Dermoscopy of a skin lesion: 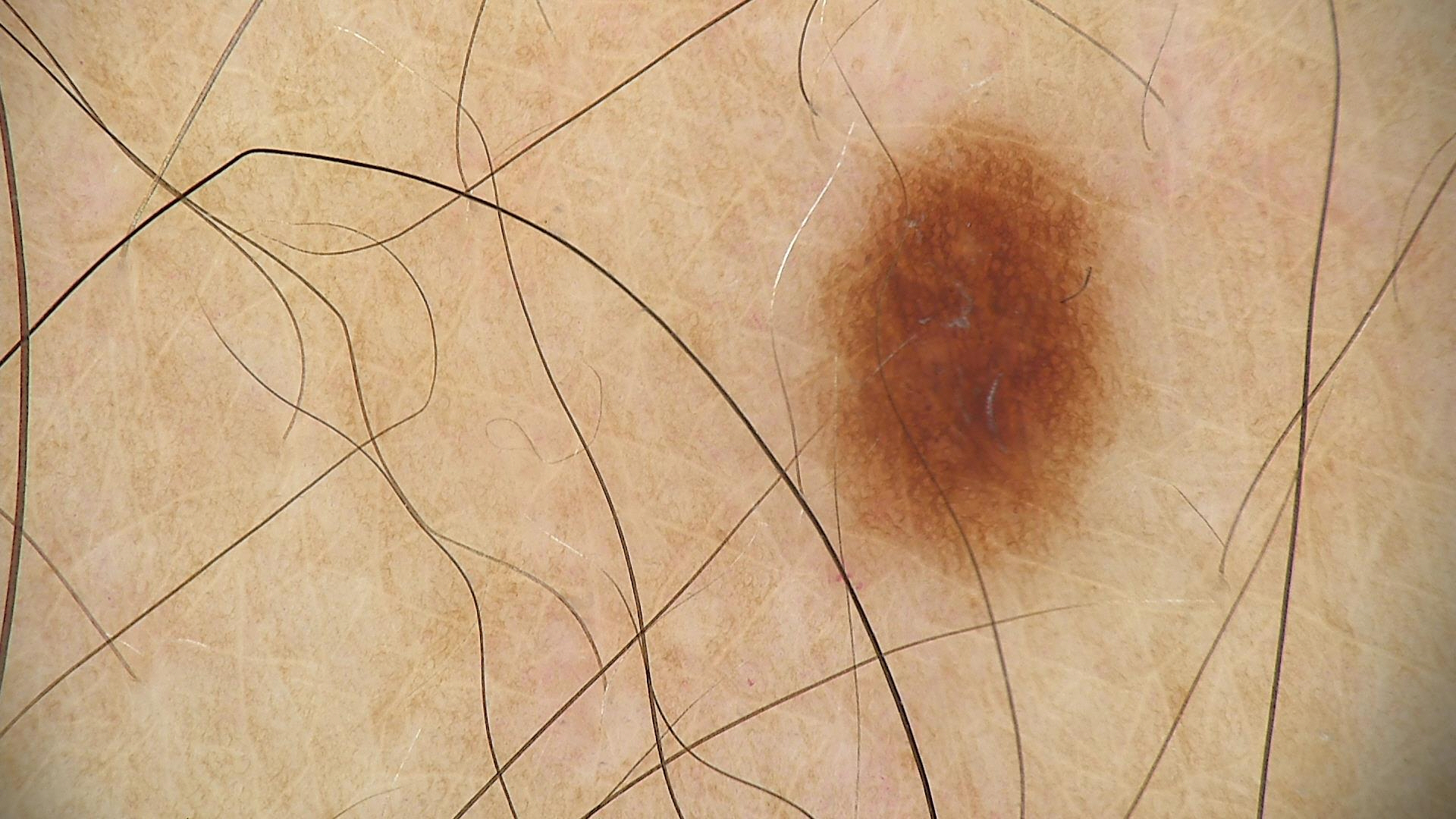{"diagnosis": {"name": "dysplastic junctional nevus", "code": "jd", "malignancy": "benign", "super_class": "melanocytic", "confirmation": "expert consensus"}}